The photo was captured at an angle; reported duration is about one day; located on the leg; the patient is male; skin tone: non-clinician graders estimated Monk skin tone scale 2 or 3: 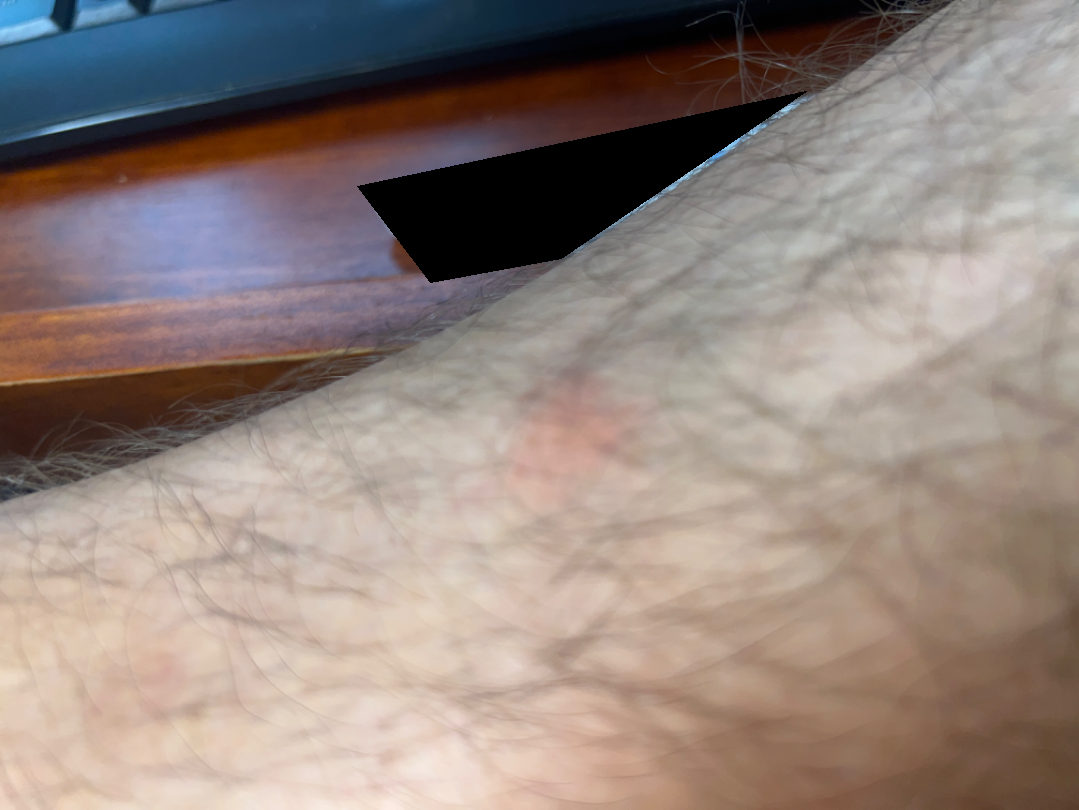Findings: On independent review by the dermatologists, in keeping with Contact dermatitis.